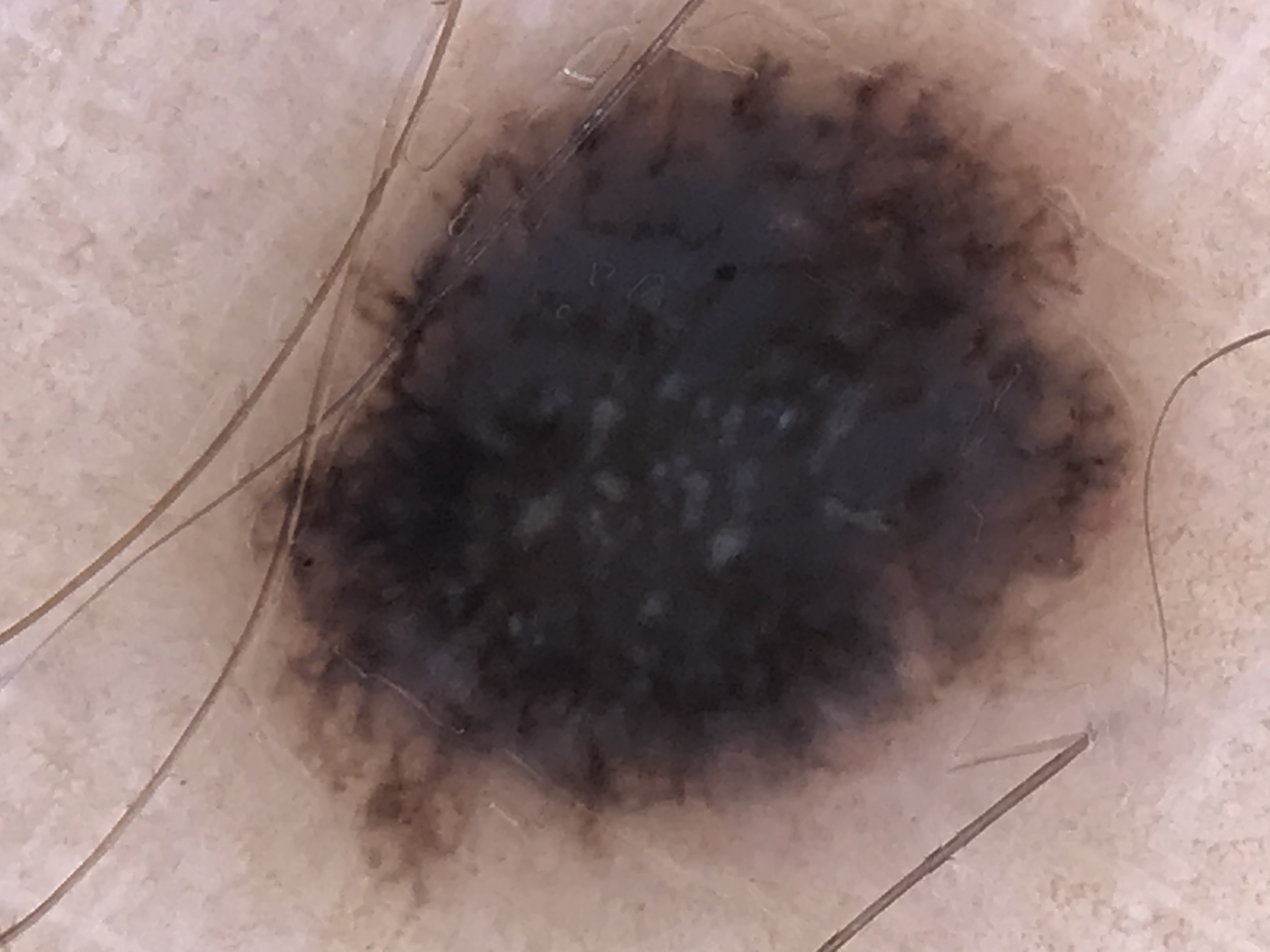A dermatoscopic image of a skin lesion. Biopsy-confirmed as a melanoma.